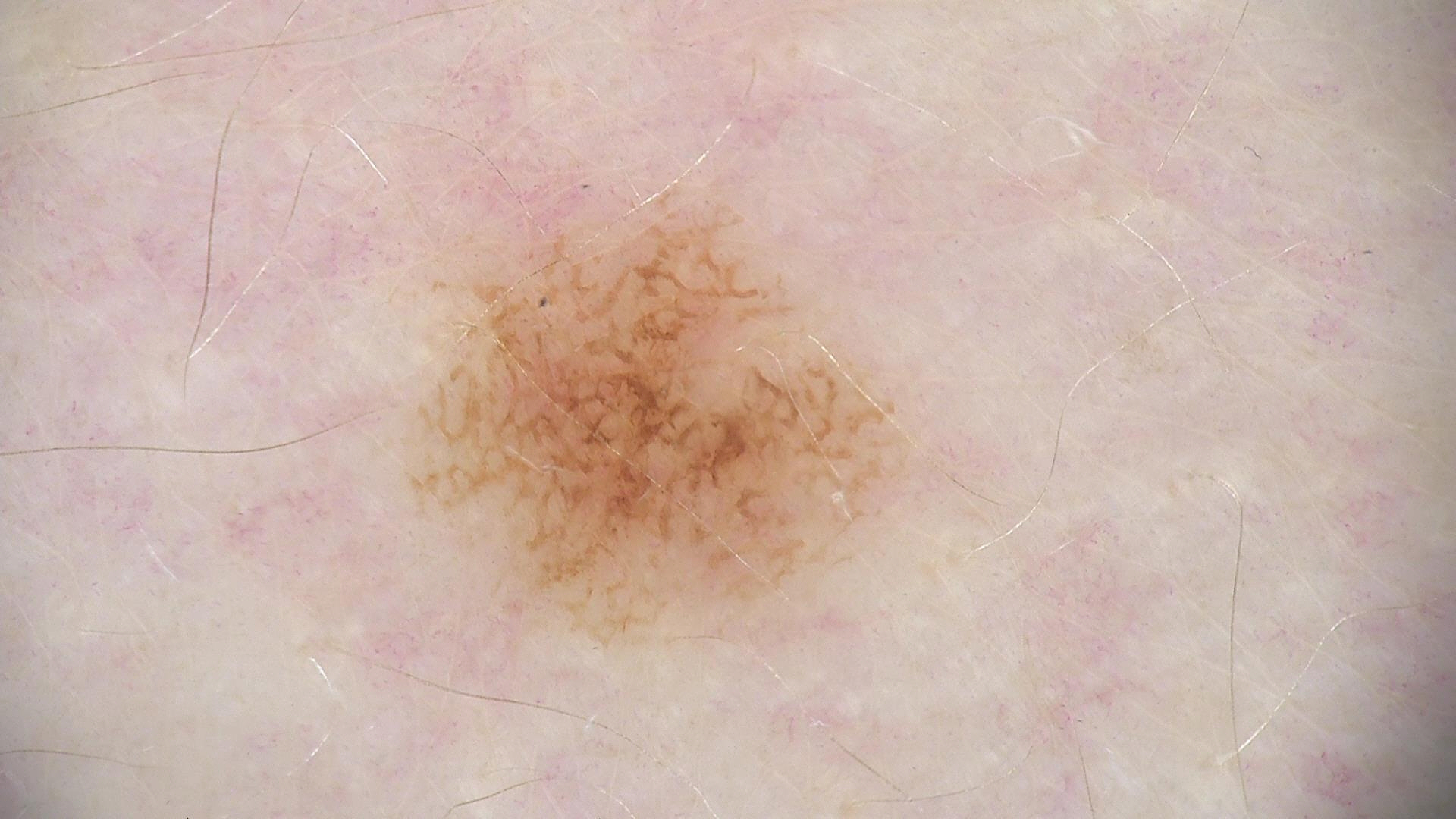A dermatoscopic image of a skin lesion. The diagnosis was a dysplastic junctional nevus.